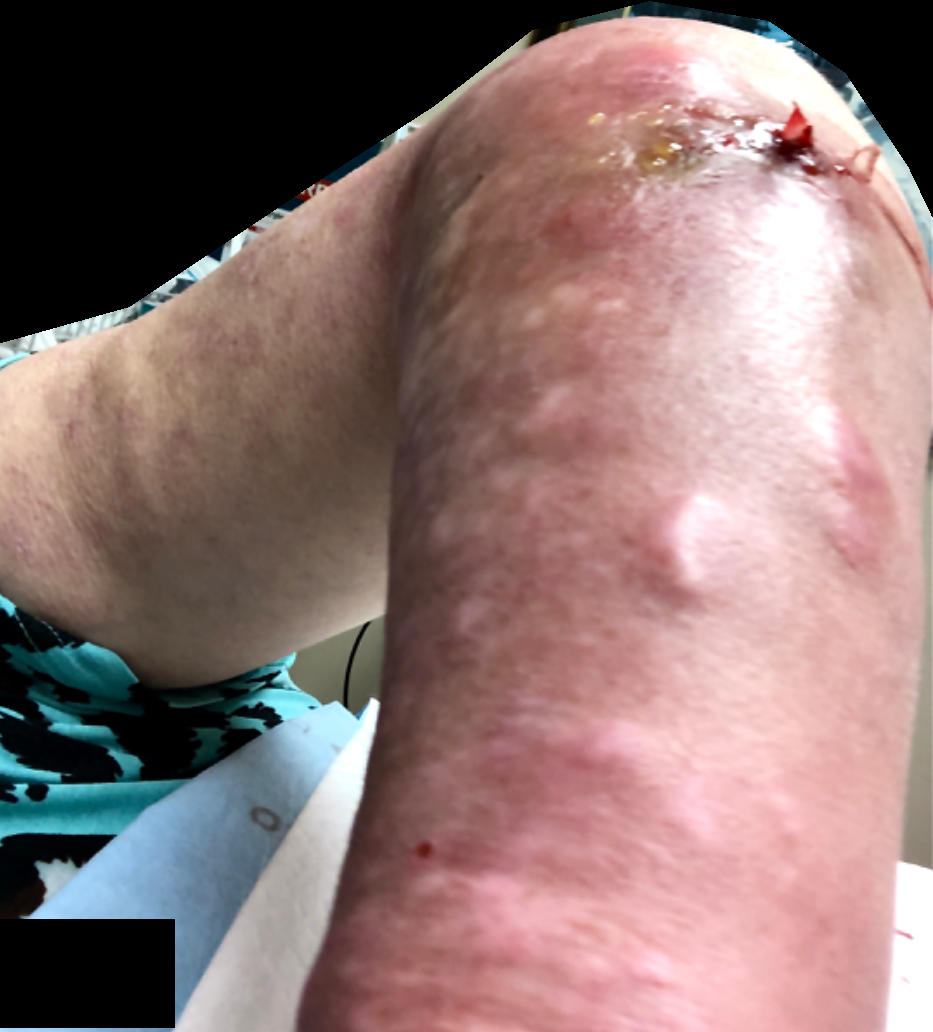Impression: The skin condition could not be confidently assessed from this image. History: Texture is reported as rough or flaky and raised or bumpy. The photo was captured at a distance. Located on the front of the torso, head or neck, arm and back of the torso. Associated systemic symptoms include fatigue and joint pain. Female contributor, age 60–69. The patient considered this a rash. Symptoms reported: bothersome appearance, enlargement and pain.